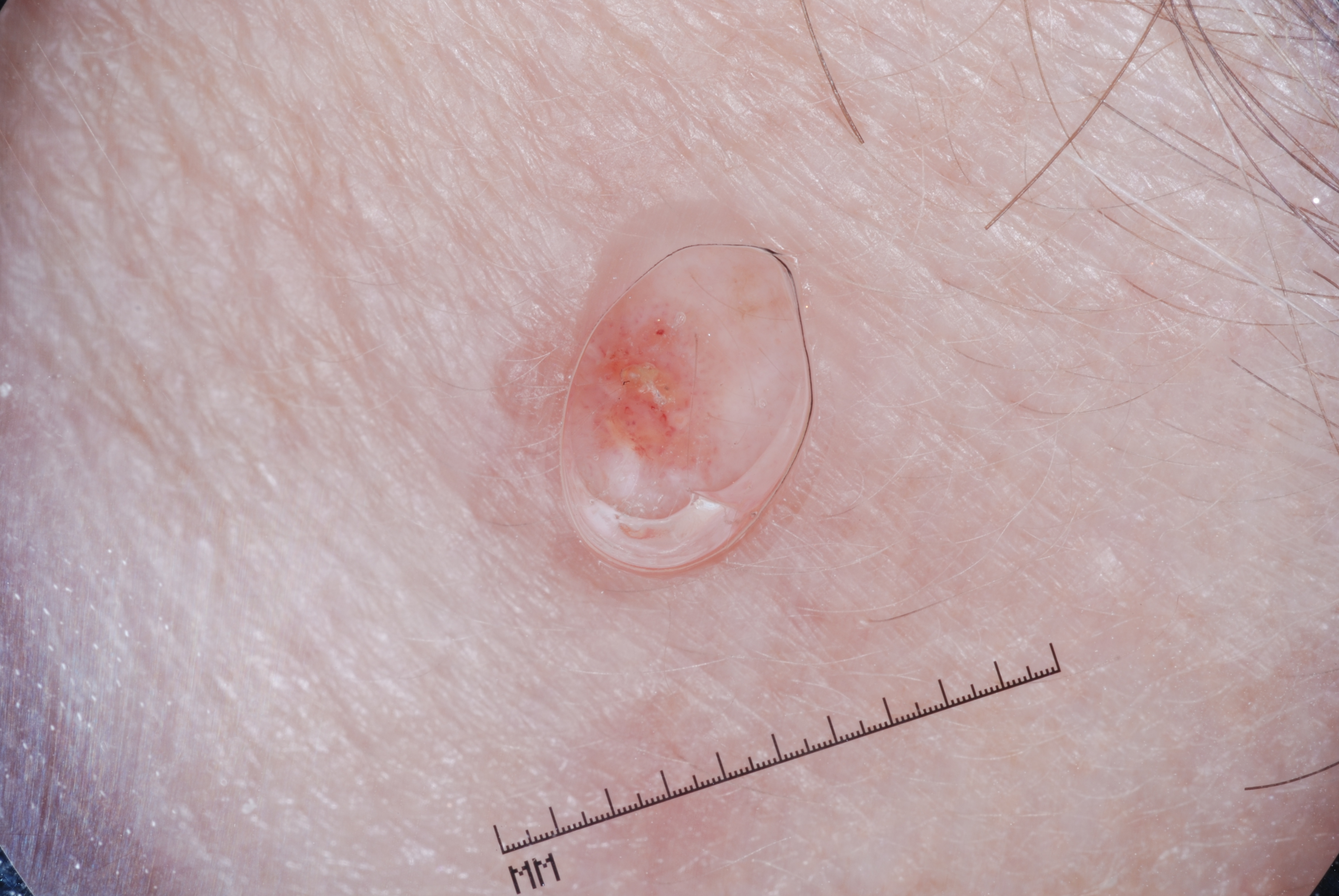{
  "image": {
    "modality": "dermoscopy"
  },
  "lesion_location": {
    "bbox_xyxy": [
      502,
      273,
      722,
      462
    ]
  },
  "dermoscopic_features": {
    "present": [],
    "absent": [
      "negative network",
      "milia-like cysts",
      "pigment network",
      "streaks"
    ]
  },
  "diagnosis": {
    "name": "seborrheic keratosis",
    "malignancy": "benign",
    "lineage": "keratinocytic",
    "provenance": "clinical"
  }
}